A dermoscopy image of a single skin lesion: 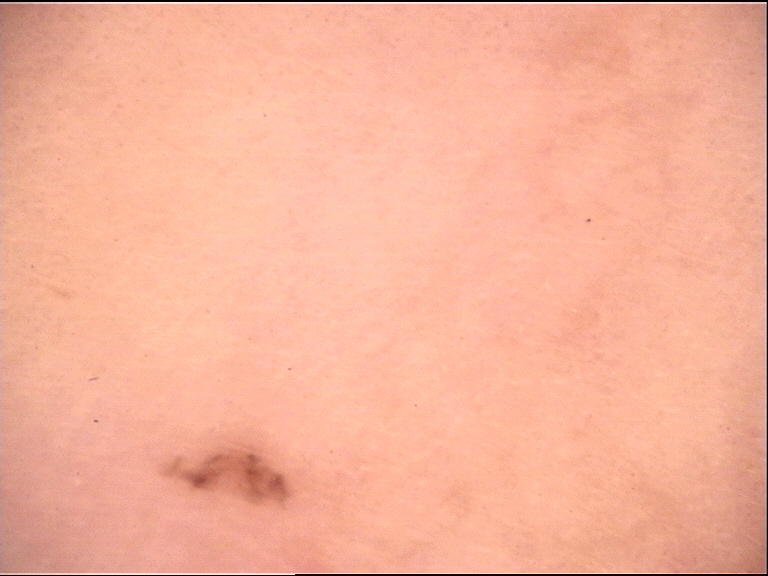assessment: dysplastic junctional nevus (expert consensus).